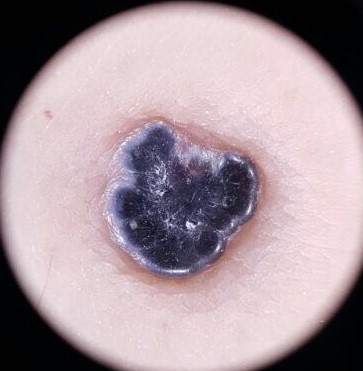lesion type=vascular
diagnosis=angiokeratoma (expert consensus)